A skin lesion imaged with a dermatoscope: 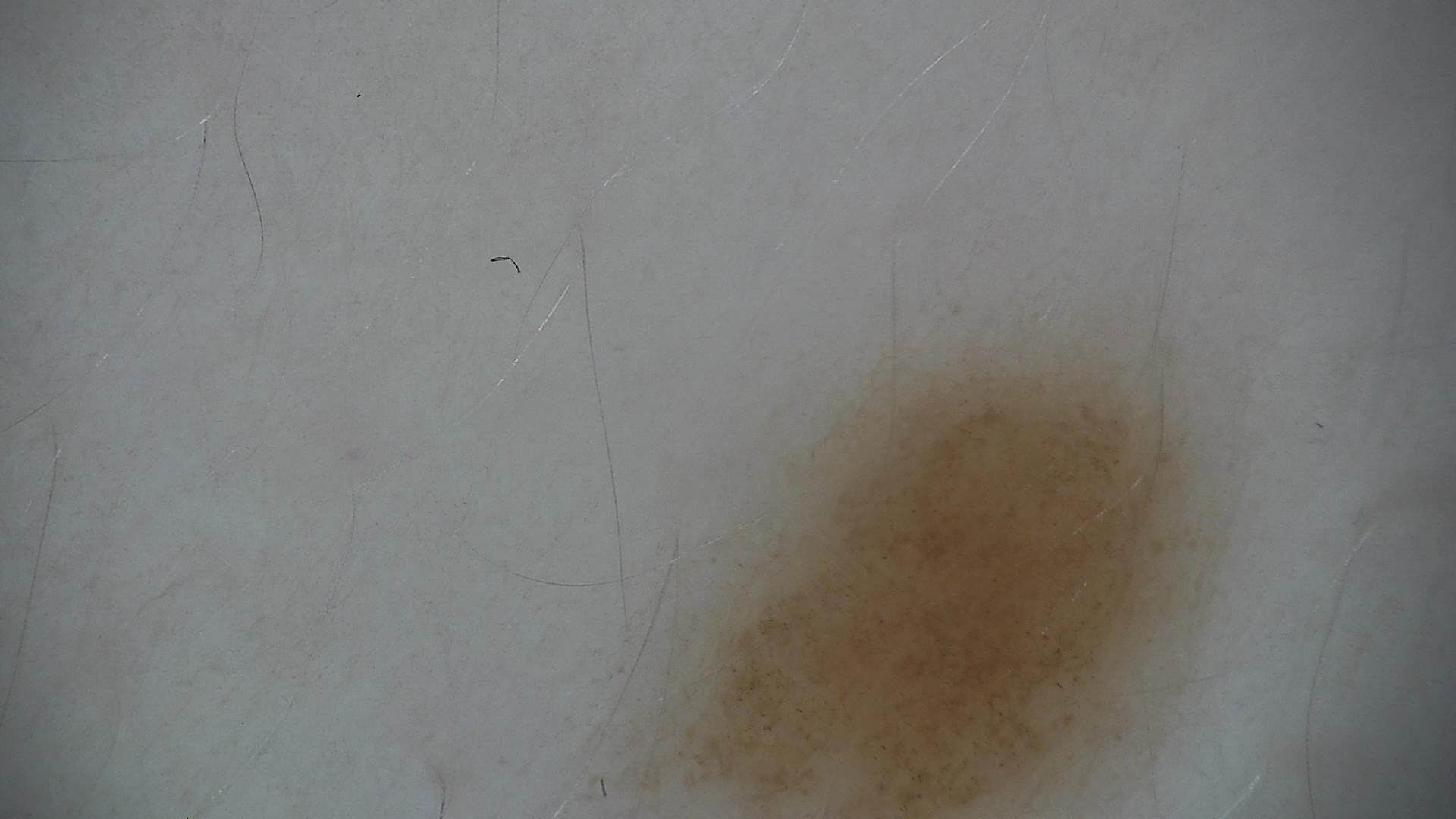The diagnosis was a benign lesion — a dysplastic junctional nevus.